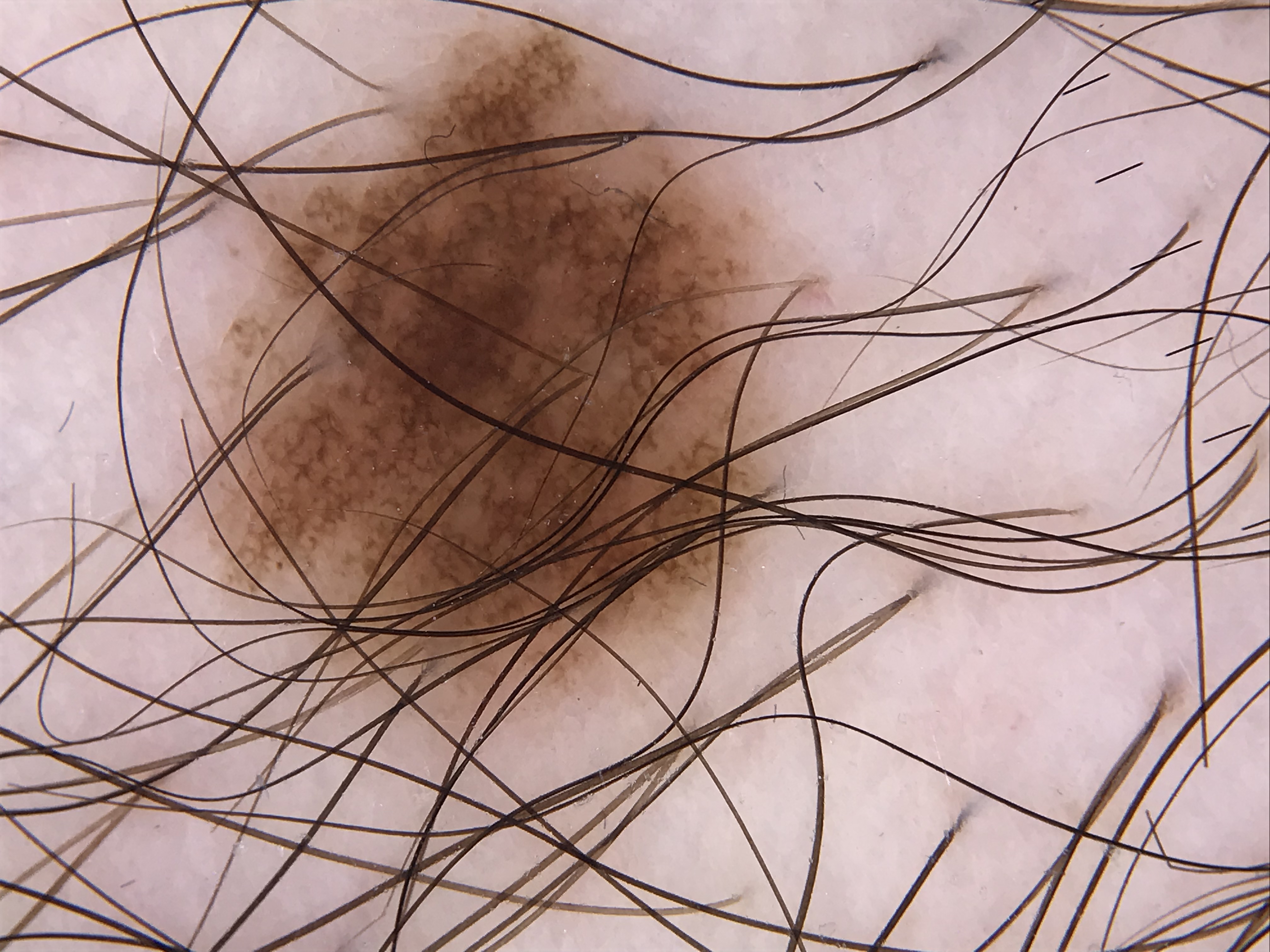Conclusion: The diagnostic label was a benign lesion — a dysplastic junctional nevus.